A female patient, in their 50s; a dermoscopic image of a skin lesion — 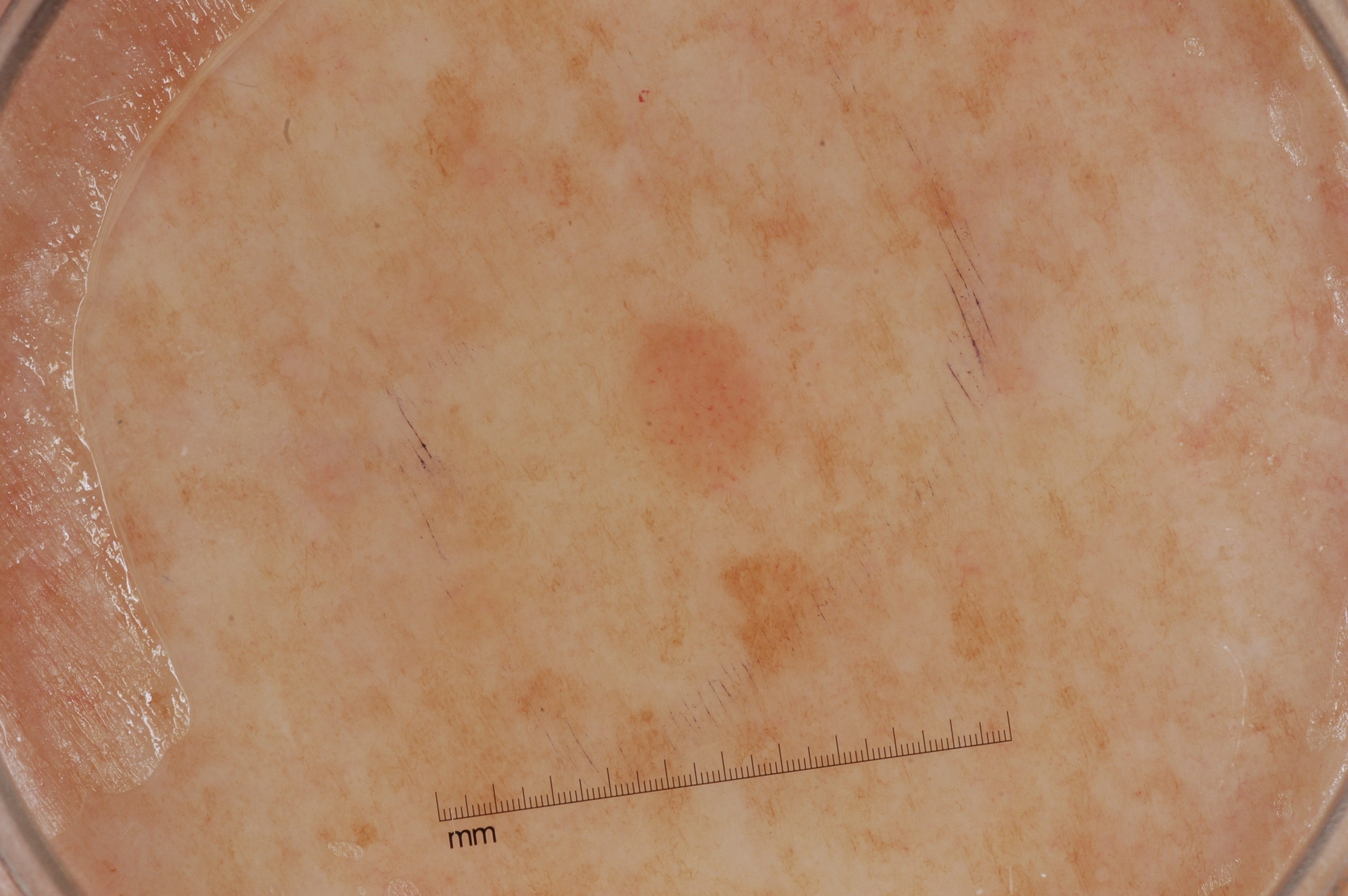Findings: As (left, top, right, bottom), the lesion is bounded by bbox=[622, 308, 778, 501]. Dermoscopic review identifies no streaks, pigment network, negative network, or milia-like cysts. Impression: The clinical diagnosis was a melanocytic nevus.